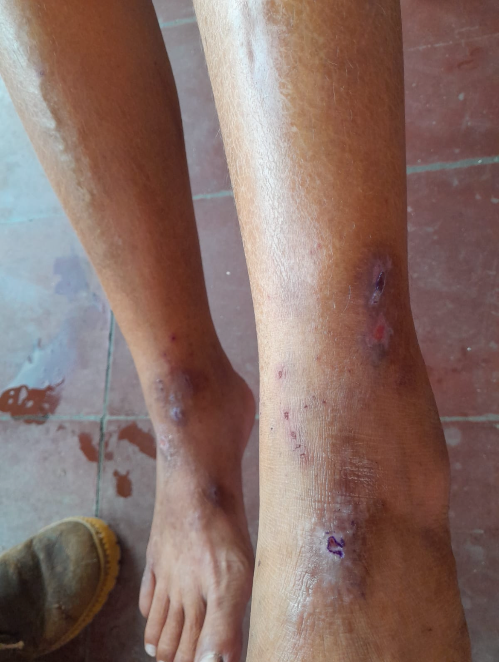The affected area is the leg, top or side of the foot and sole of the foot. Close-up view. The contributor is 40–49, female. Single-reviewer assessment: most consistent with Lichen Simplex Chronicus; the differential also includes Eczema; less probable is Lichen planus/lichenoid eruption.